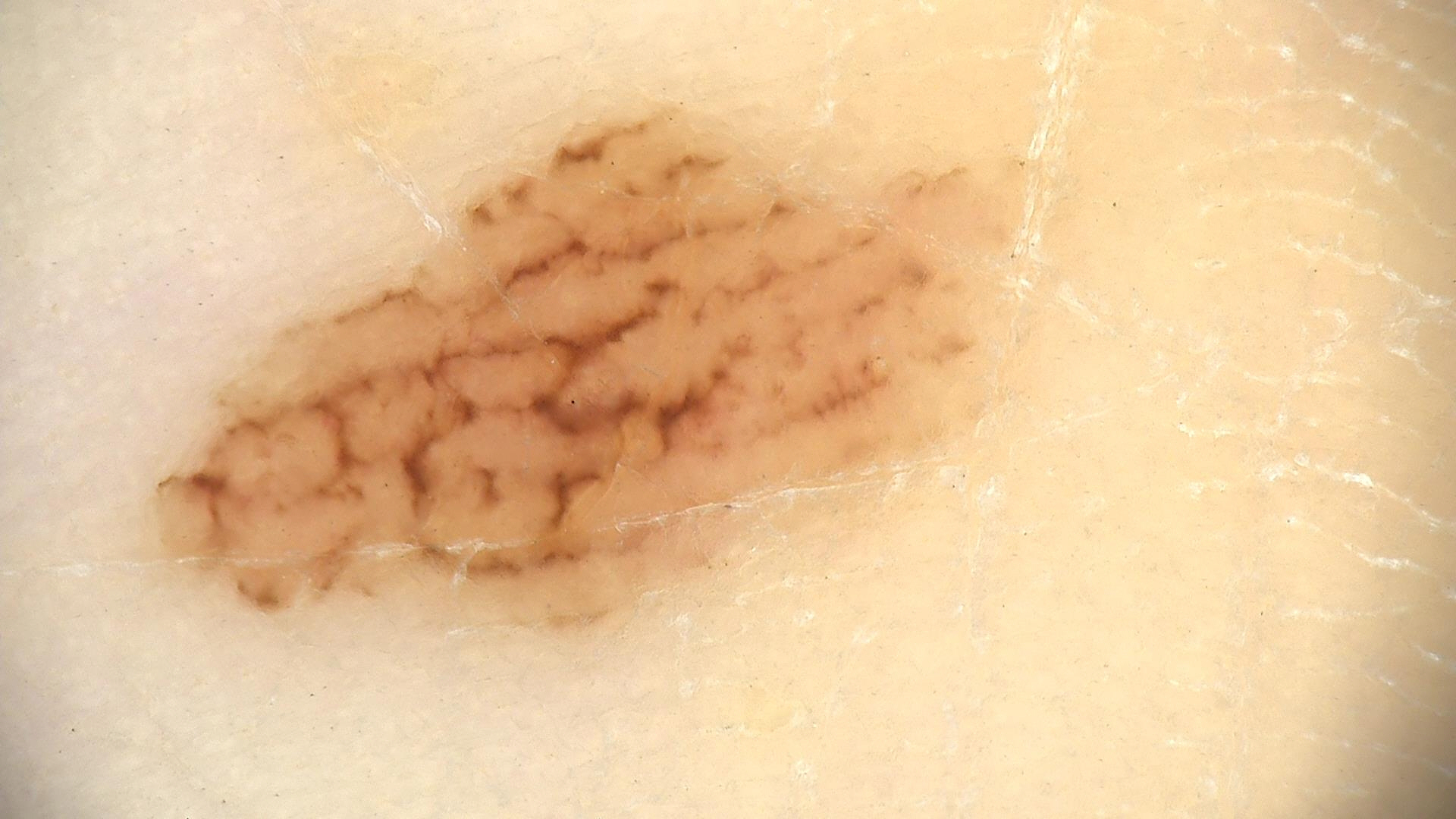The diagnostic label was an acral compound nevus.